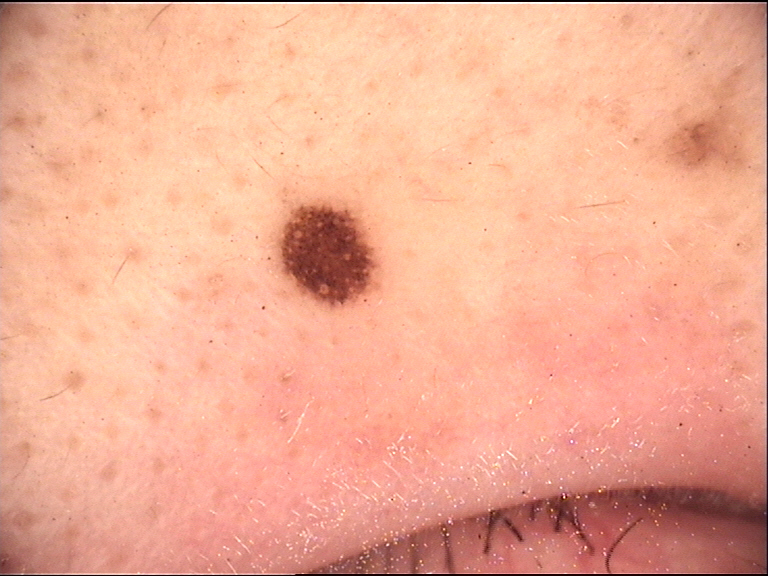Findings:
– class — Miescher nevus (expert consensus)